A male patient aged 65; numerous moles by the patient's own estimate; the patient says their skin reddens painfully with sun exposure; the patient reports a family history of skin cancer, a personal history of skin cancer, immunosuppression, no prior organ transplant, and no sunbed use; a clinical photograph showing a skin lesion:
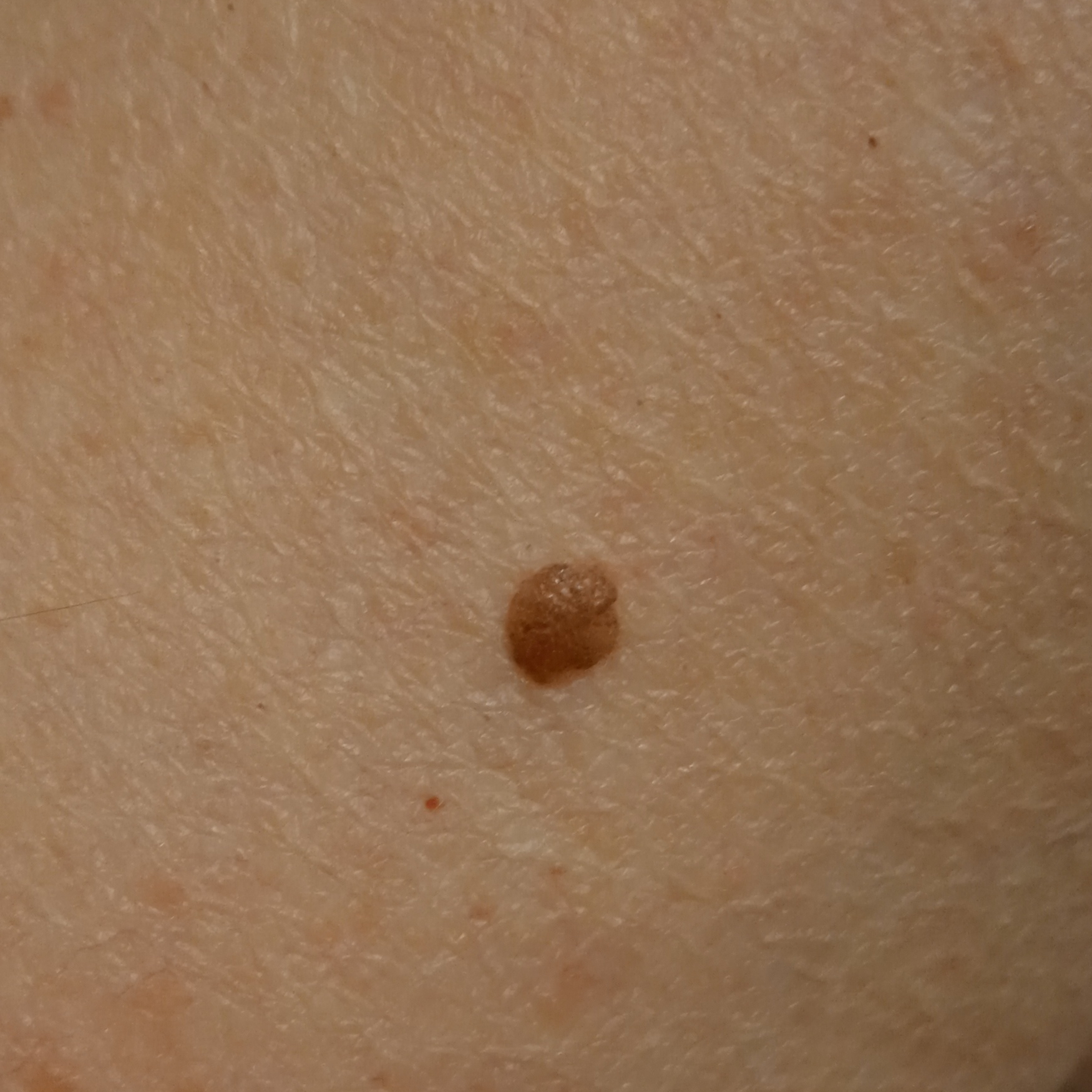The lesion is located on an arm. The lesion is about 3 mm across. The consensus diagnosis for this lesion was a melanocytic nevus.